The photo was captured at a distance. The lesion involves the top or side of the foot. The subject is female.
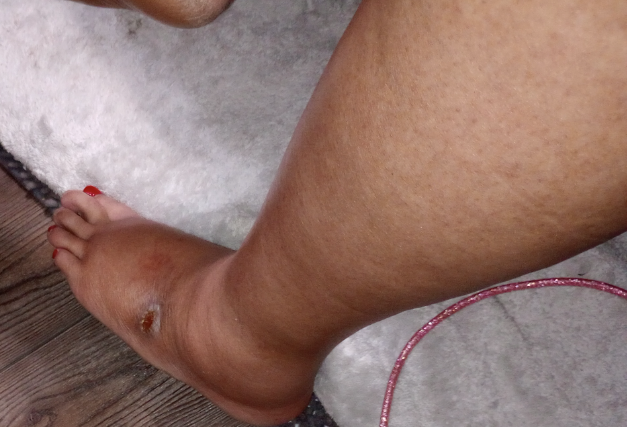Q: What conditions are considered?
A: Foot ulcer and Stasis Dermatitis were considered with similar weight; possibly Leukocytoclastic Vasculitis